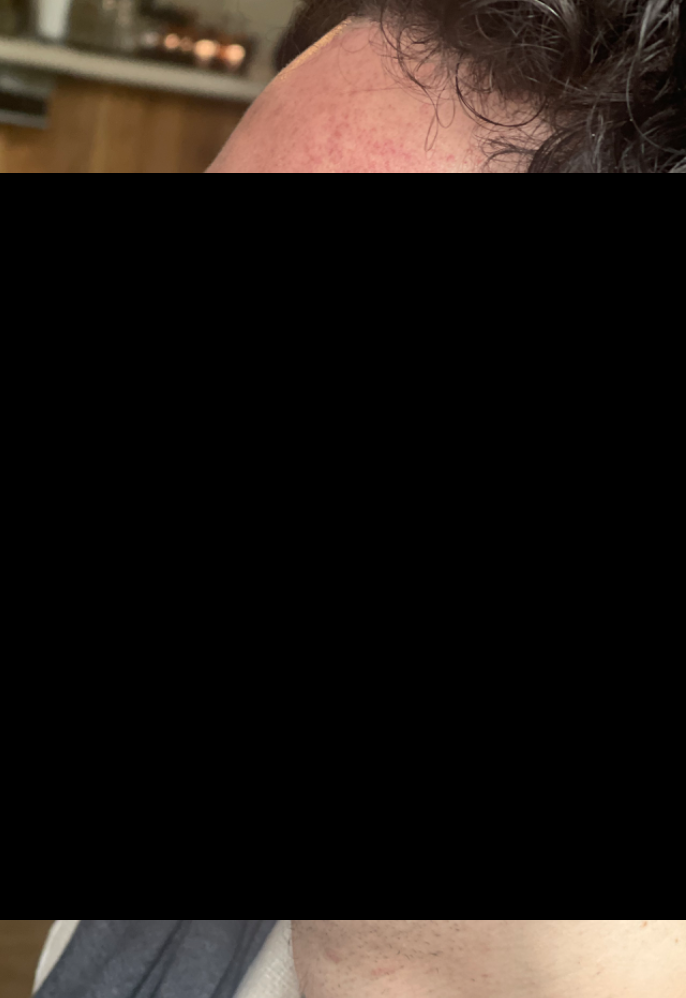{
  "body_site": "head or neck",
  "symptoms": "bothersome appearance",
  "skin_tone": {
    "monk_skin_tone": 2
  },
  "texture": "flat",
  "shot_type": "at a distance",
  "patient_category": "a rash",
  "differential": {
    "leading": [
      "Rosacea"
    ],
    "considered": [
      "Acne"
    ]
  }
}